A dermatoscopic image of a skin lesion: 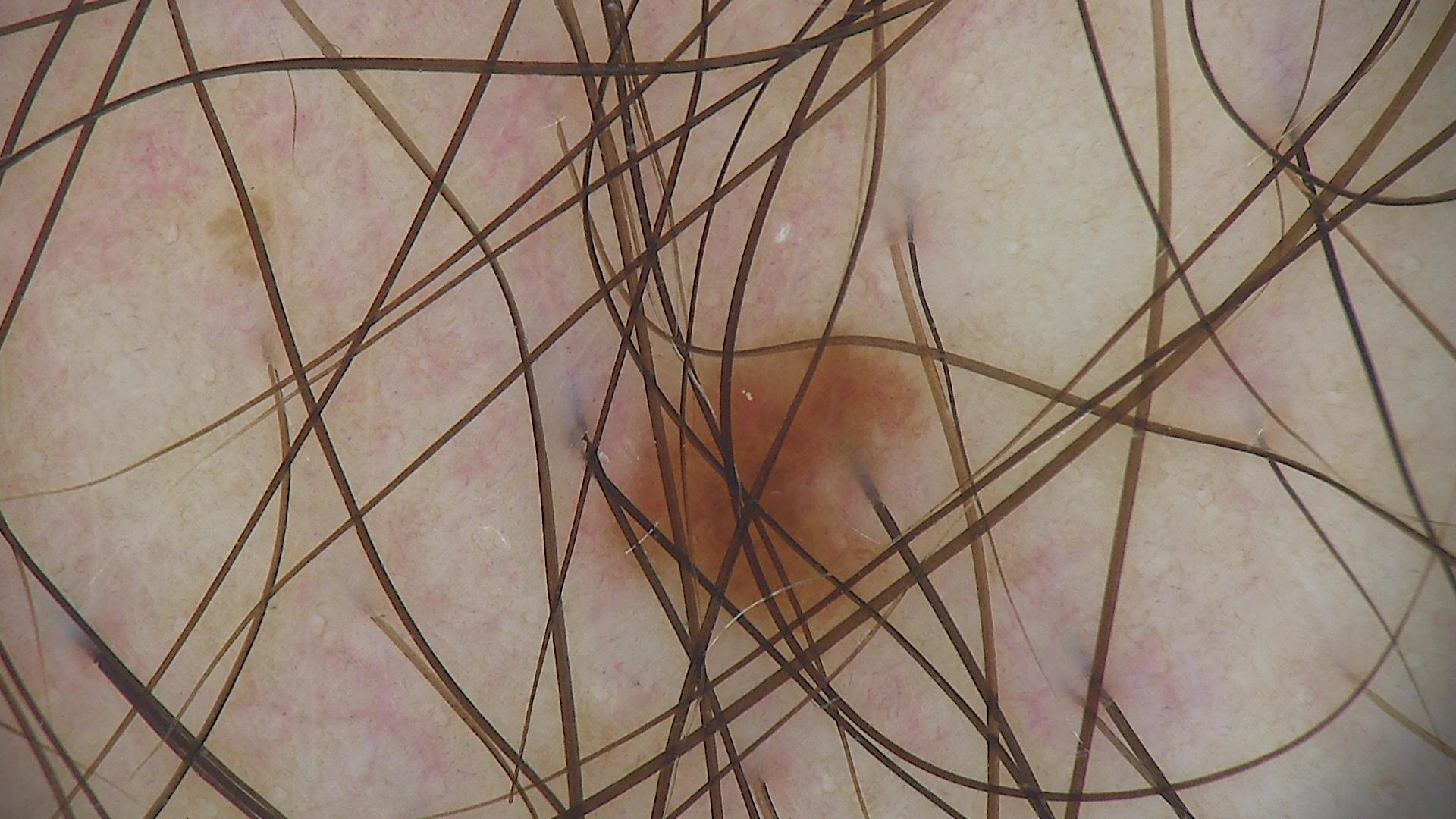This is a banal lesion. The diagnosis was a junctional nevus.